A dermoscopy image of a single skin lesion.
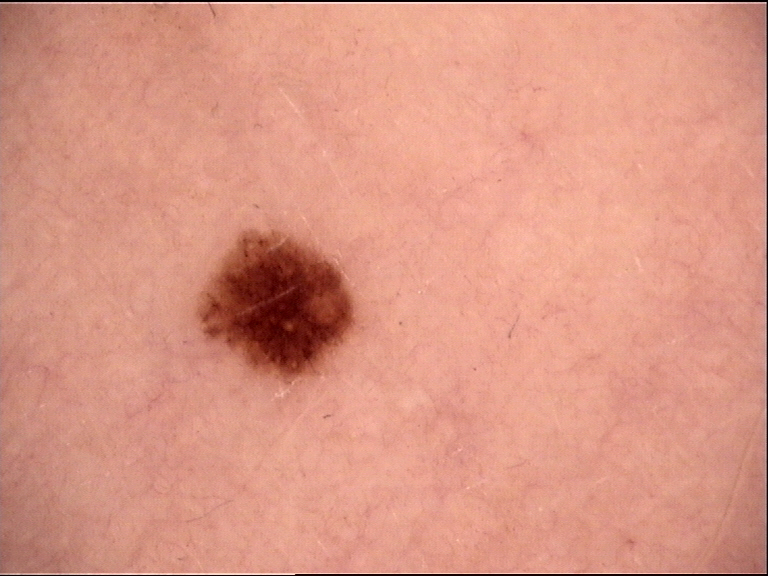Summary: The morphology is that of a banal lesion. Conclusion: The diagnostic label was a junctional nevus.